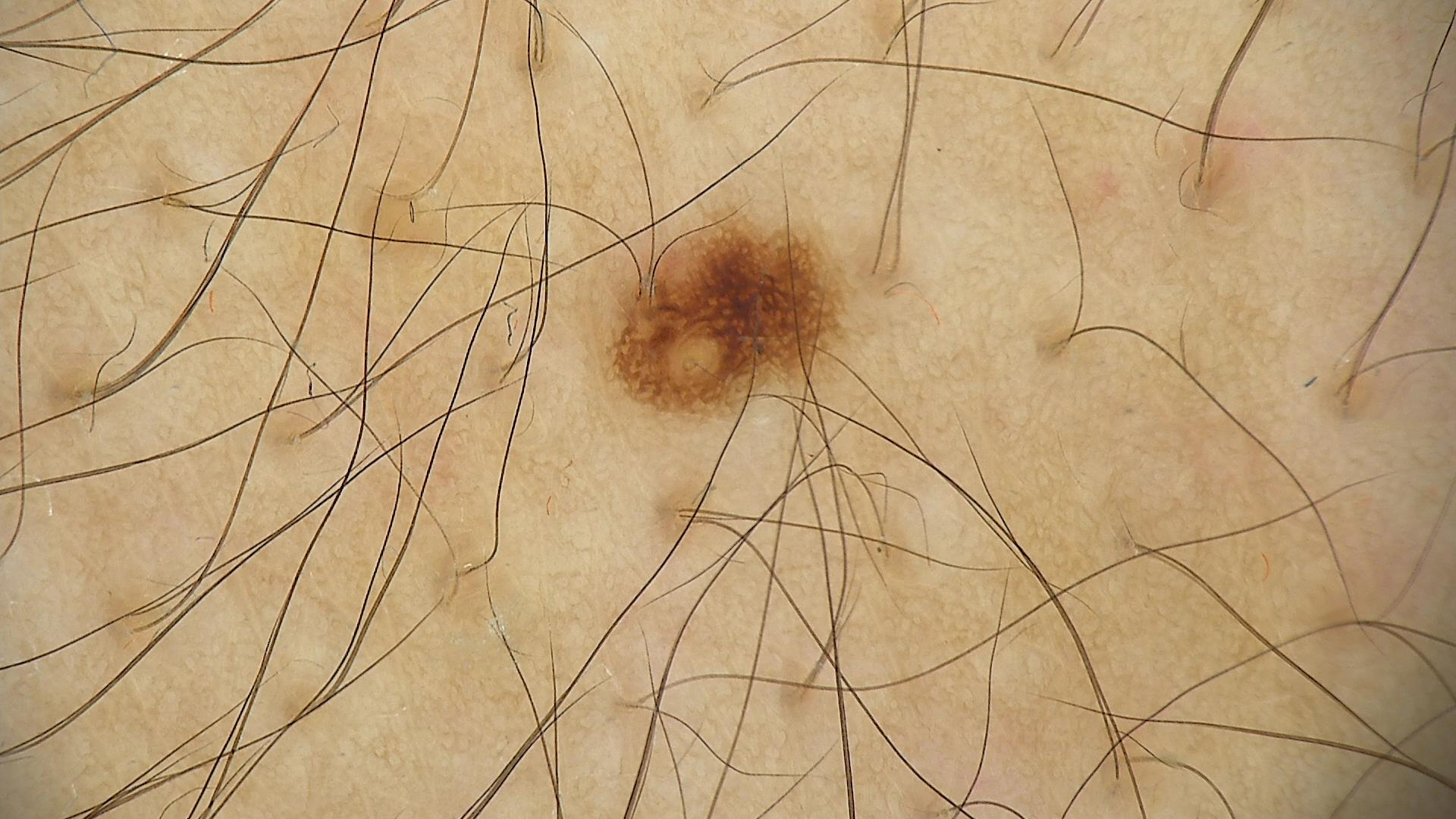The diagnosis was a benign lesion — a dysplastic junctional nevus.